Imaged for a research study, with no referral diagnosis recorded; on a questionnaire the patient reported a personal history of cancer; a male subject 73 years of age; the patient says their skin reddens with sun exposure; a skin lesion imaged with a dermatoscope: 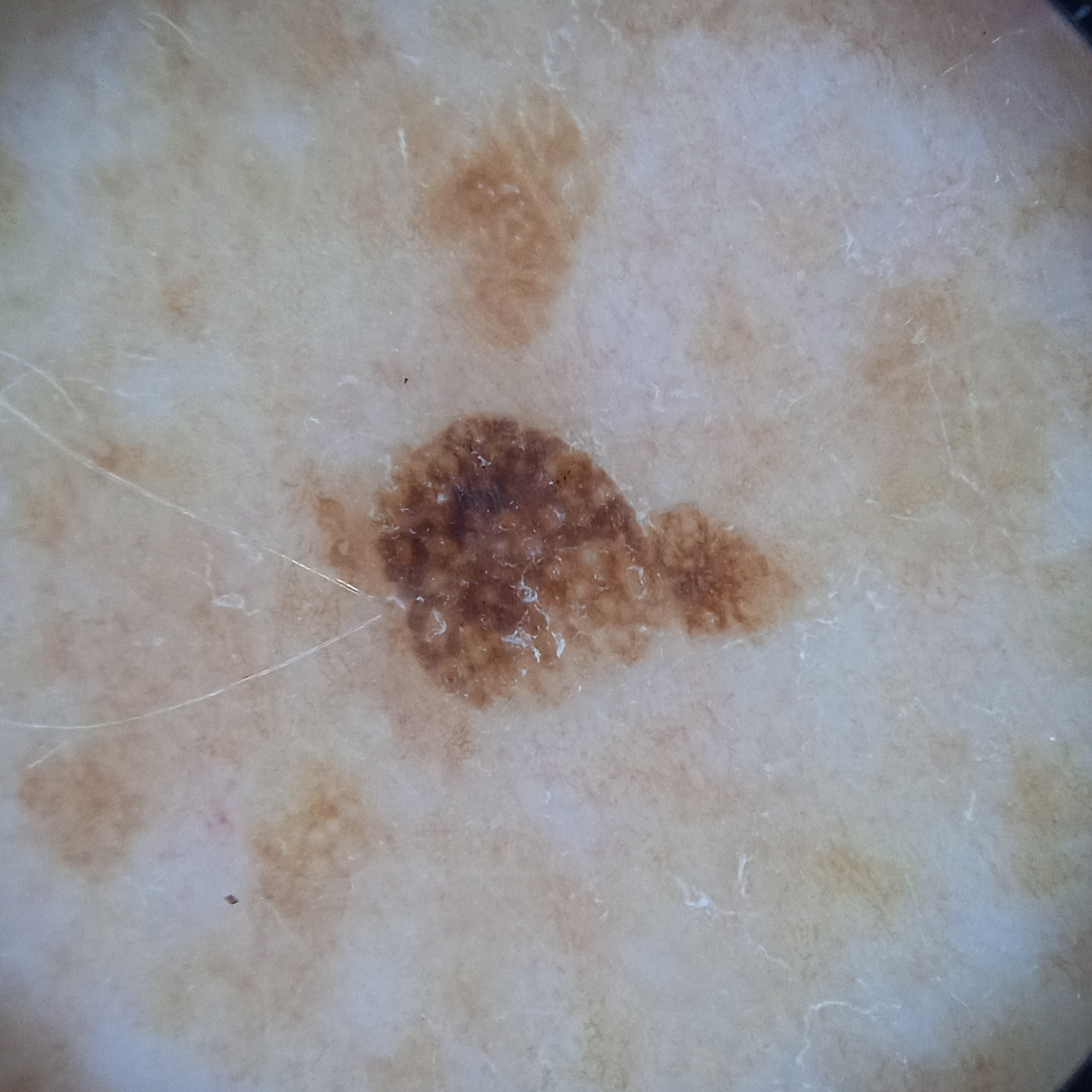Case summary:
The lesion is on the back. Measuring roughly 5.5 mm.
Impression:
The dermatologists' assessment was a seborrheic keratosis.